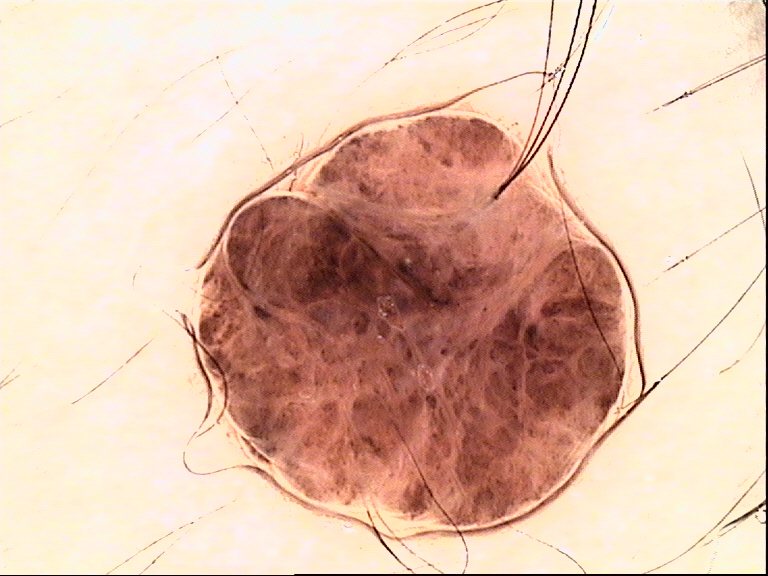A skin lesion imaged with a dermatoscope. Diagnosed as a dermal nevus.